A dermoscopic image of a skin lesion.
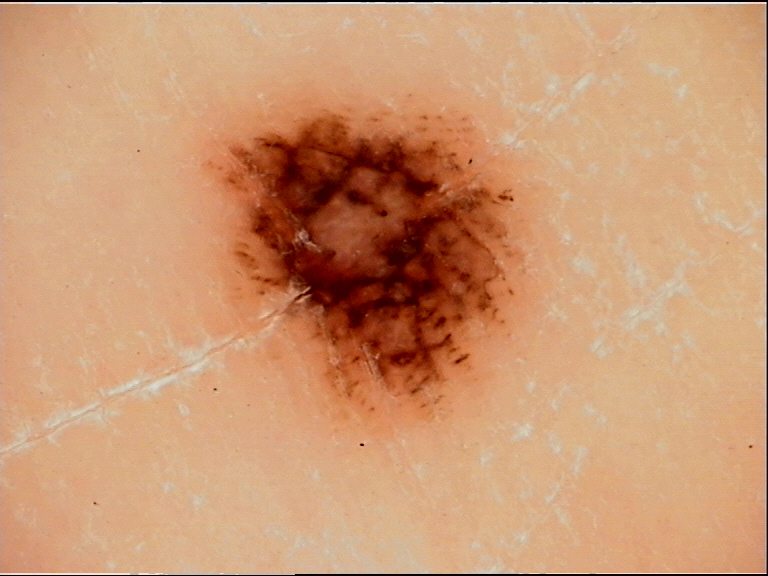Diagnosis:
Confirmed on histopathology as an acral lentiginous melanoma.